Skin tone: Fitzpatrick phototype III; lay graders estimated MST 3–4 · the arm is involved · this image was taken at a distance · reported lesion symptoms include itching — 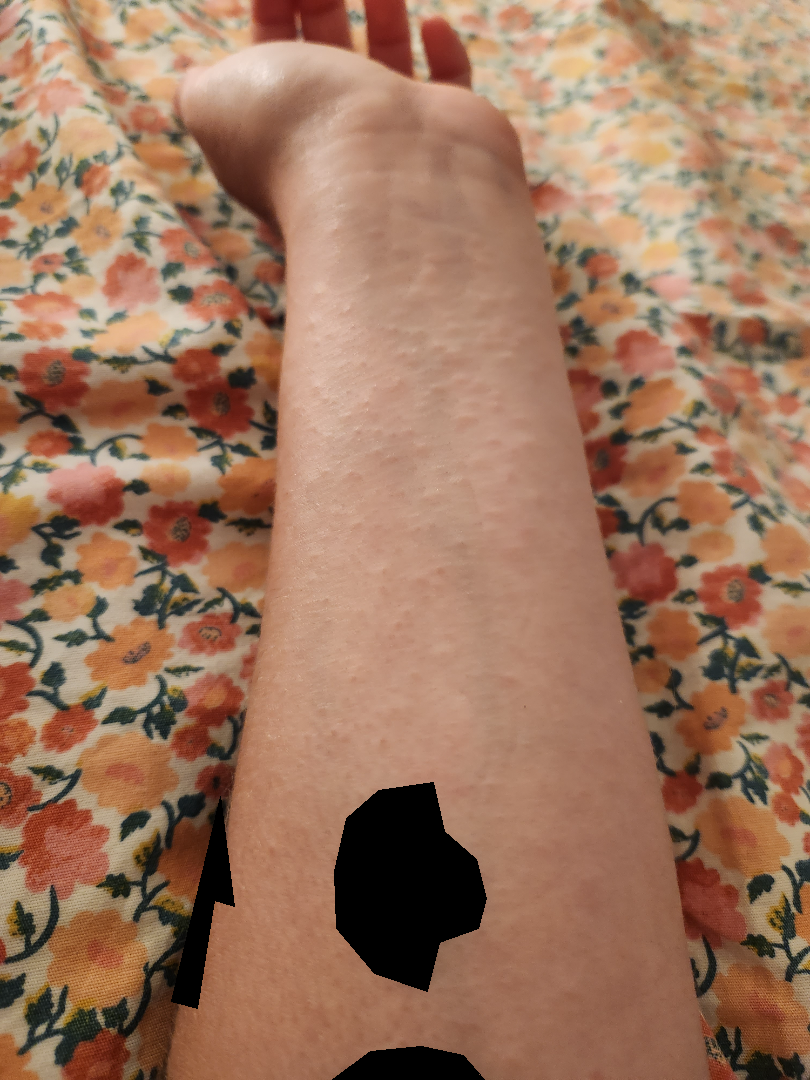assessment: ungradable on photographic review.